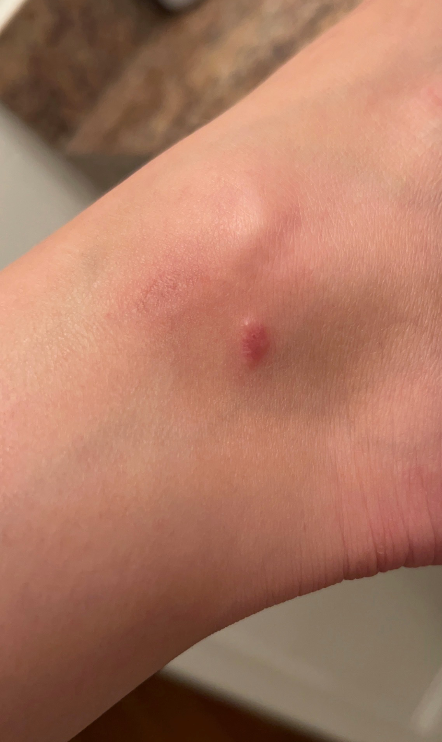Impression: A single dermatologist reviewed the case: most consistent with Insect Bite; the differential also includes Dermatofibroma; a more distant consideration is Skin cancer.